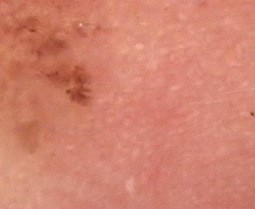{"image": "dermoscopy", "diagnosis": {"name": "basal cell carcinoma", "code": "bcc", "malignancy": "malignant", "super_class": "non-melanocytic", "confirmation": "histopathology"}}